This is a dermoscopic photograph of a skin lesion.
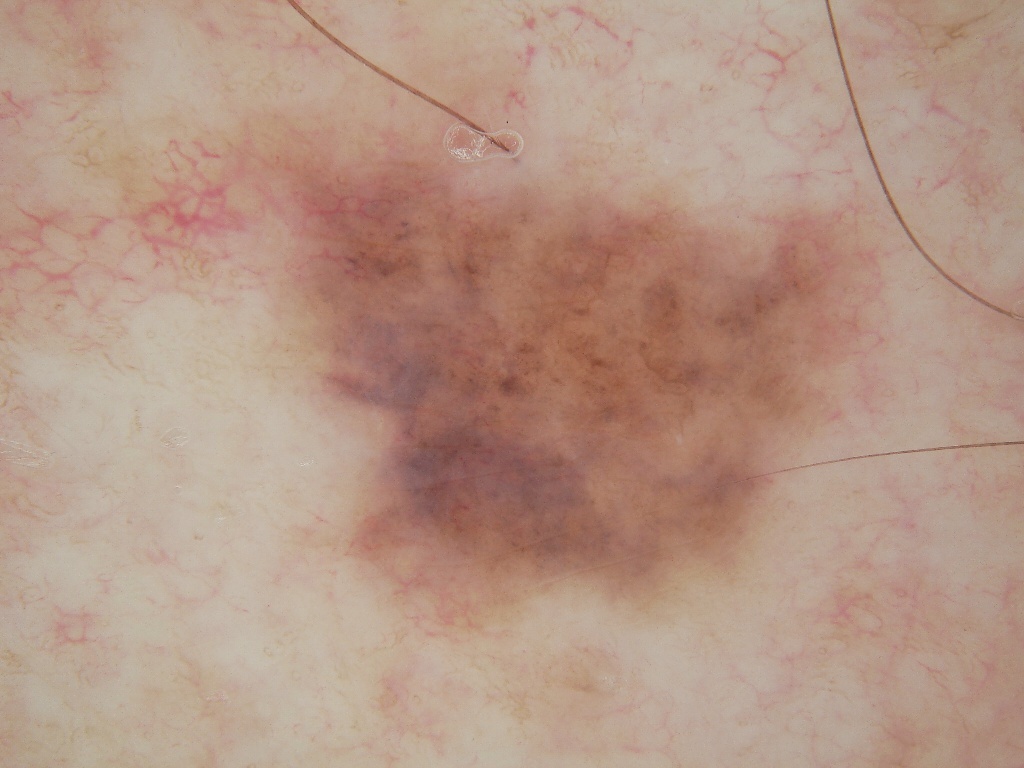Dermoscopy demonstrates no milia-like cysts, pigment network, negative network, globules, or streaks. The lesion is bounded by <box>151, 56, 910, 663</box>. Expert review diagnosed this as a melanocytic nevus.